The photo was captured at an angle · located on the leg, arm and back of the hand — 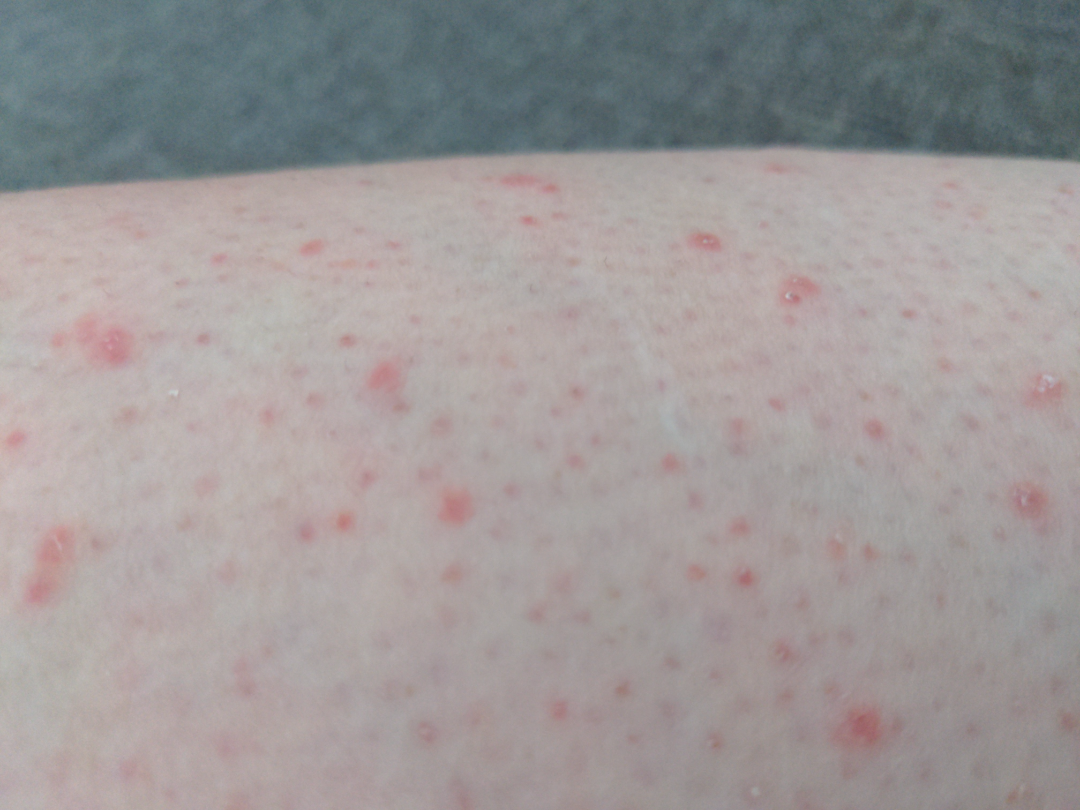- diagnostic considerations: the leading impression is Folliculitis